A clinical photograph showing a skin lesion; a female patient in their 50s:
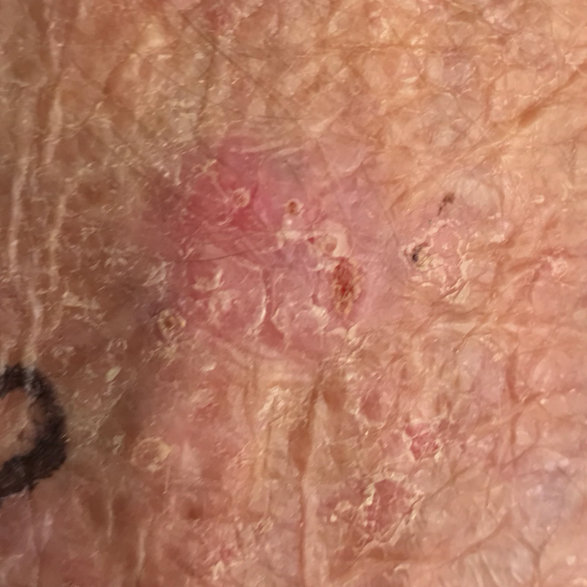Q: Where on the body is the lesion?
A: a hand
Q: Any reported symptoms?
A: bleeding, itching, growth, elevation
Q: What is this lesion?
A: basal cell carcinoma (biopsy-proven)